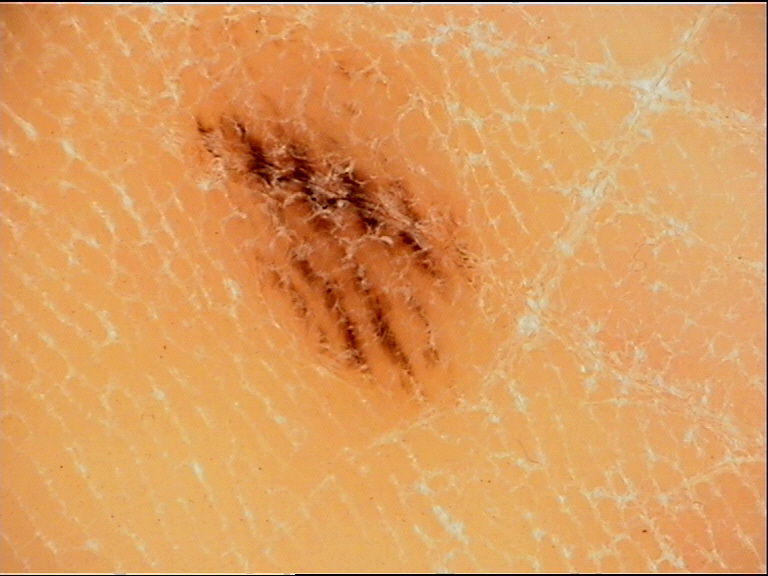The diagnosis was an acral dysplastic junctional nevus.